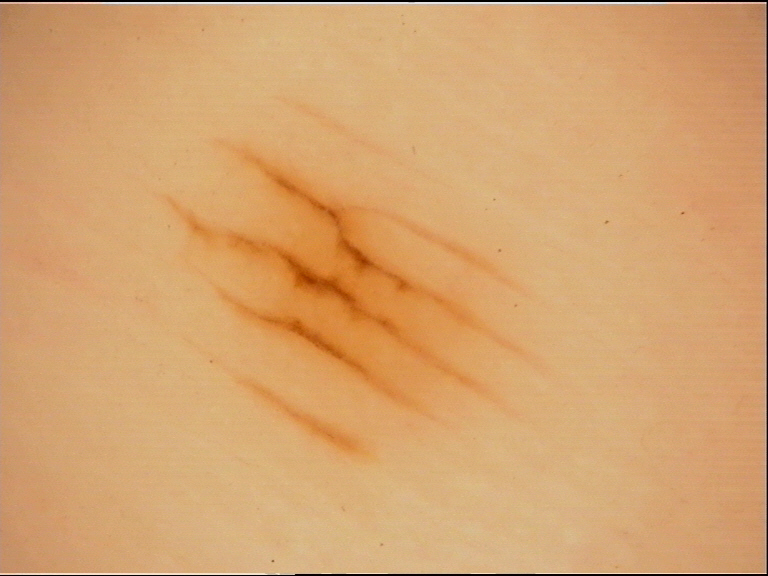Summary:
A dermoscopic image of a skin lesion.
Impression:
Diagnosed as an acral junctional nevus.